A dermoscopic photograph of a skin lesion.
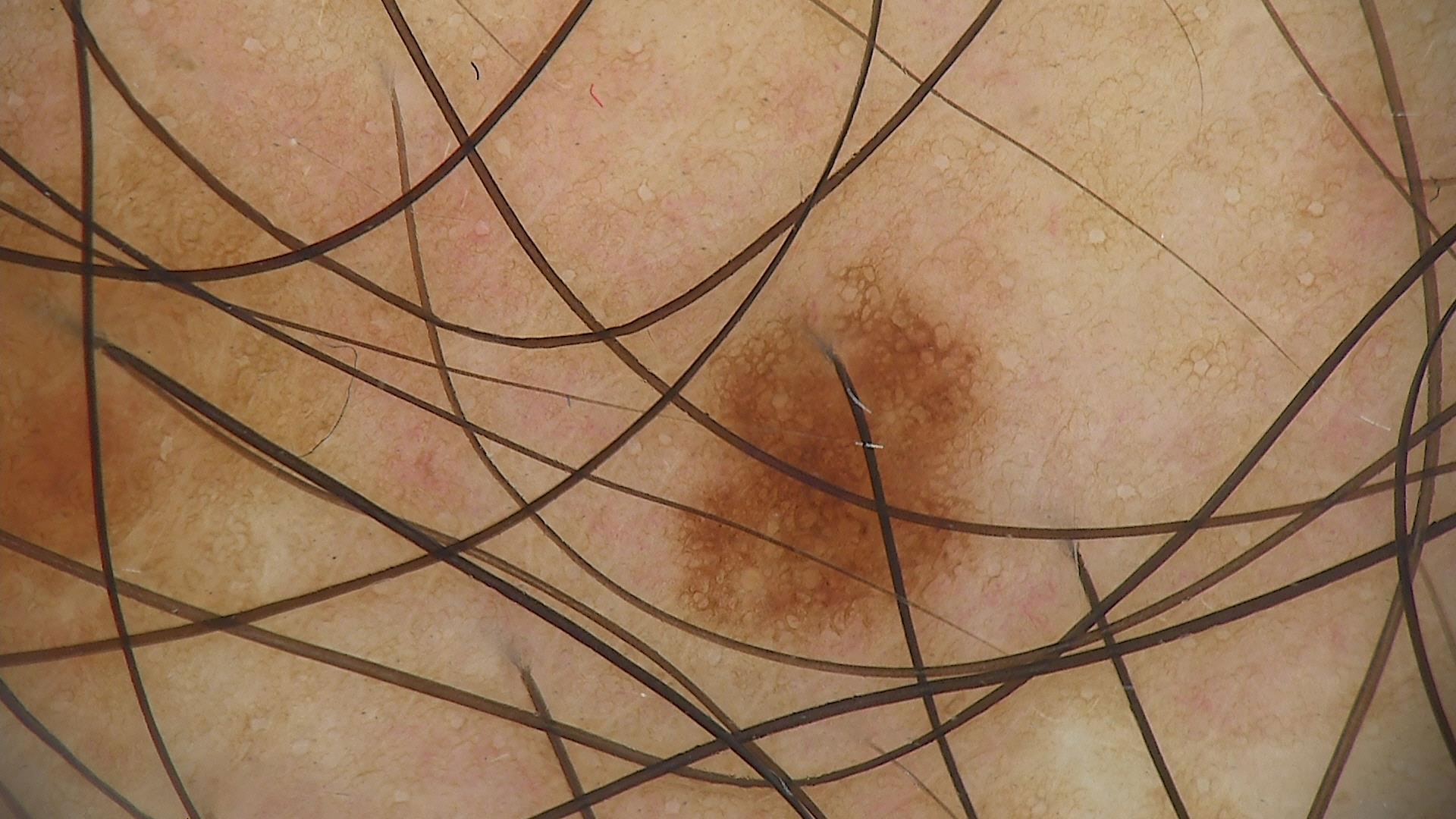The diagnostic label was a dysplastic junctional nevus.